FST III; lay reviewers estimated MST 2. The affected area is the leg. The lesion is associated with enlargement, bothersome appearance and itching. The photo was captured at an angle. Reported duration is one to three months. The patient considered this a rash.
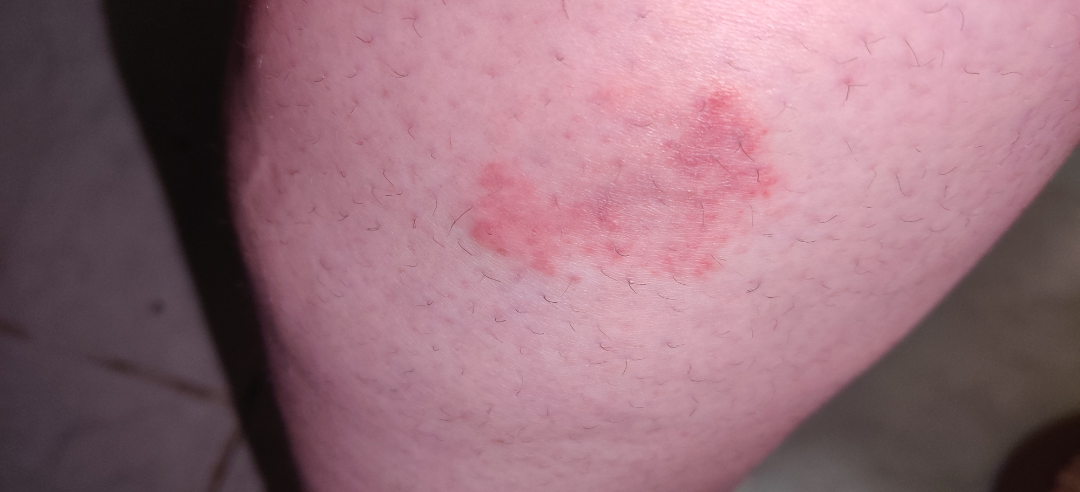The skin condition could not be confidently assessed from this image.